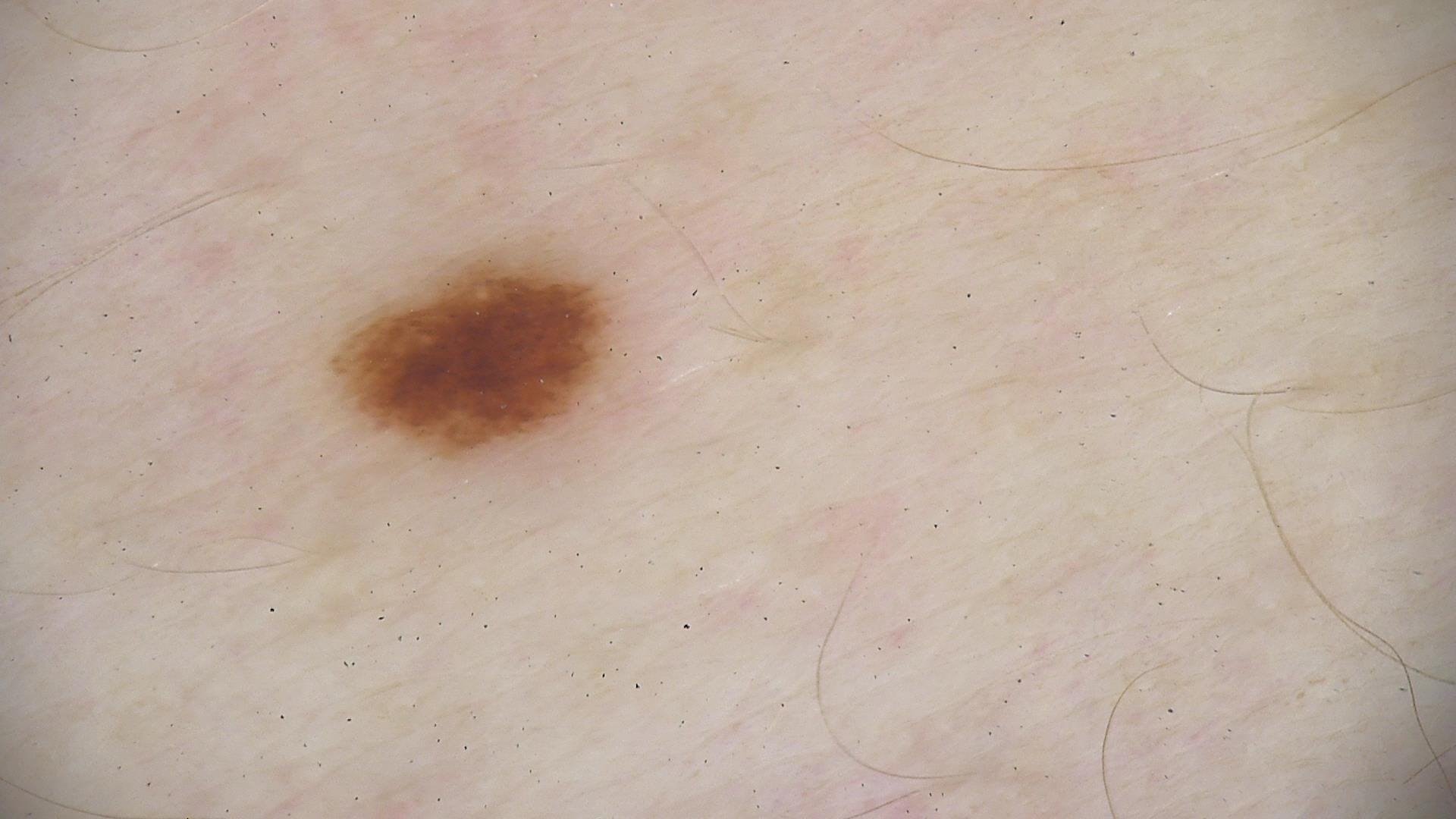Consistent with a dysplastic junctional nevus.